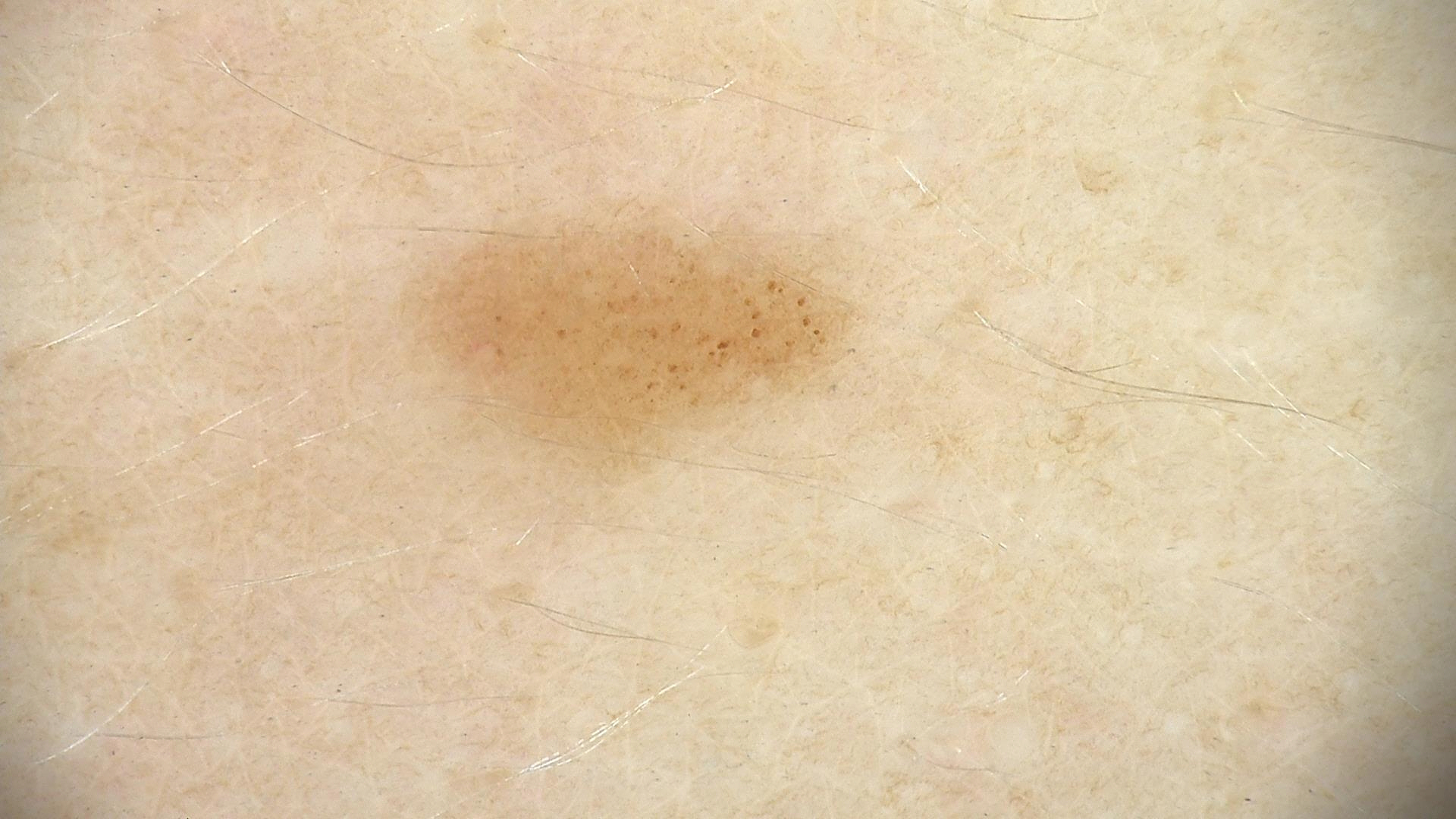Q: What is the imaging modality?
A: dermatoscopy
Q: What is the diagnosis?
A: dysplastic junctional nevus (expert consensus)